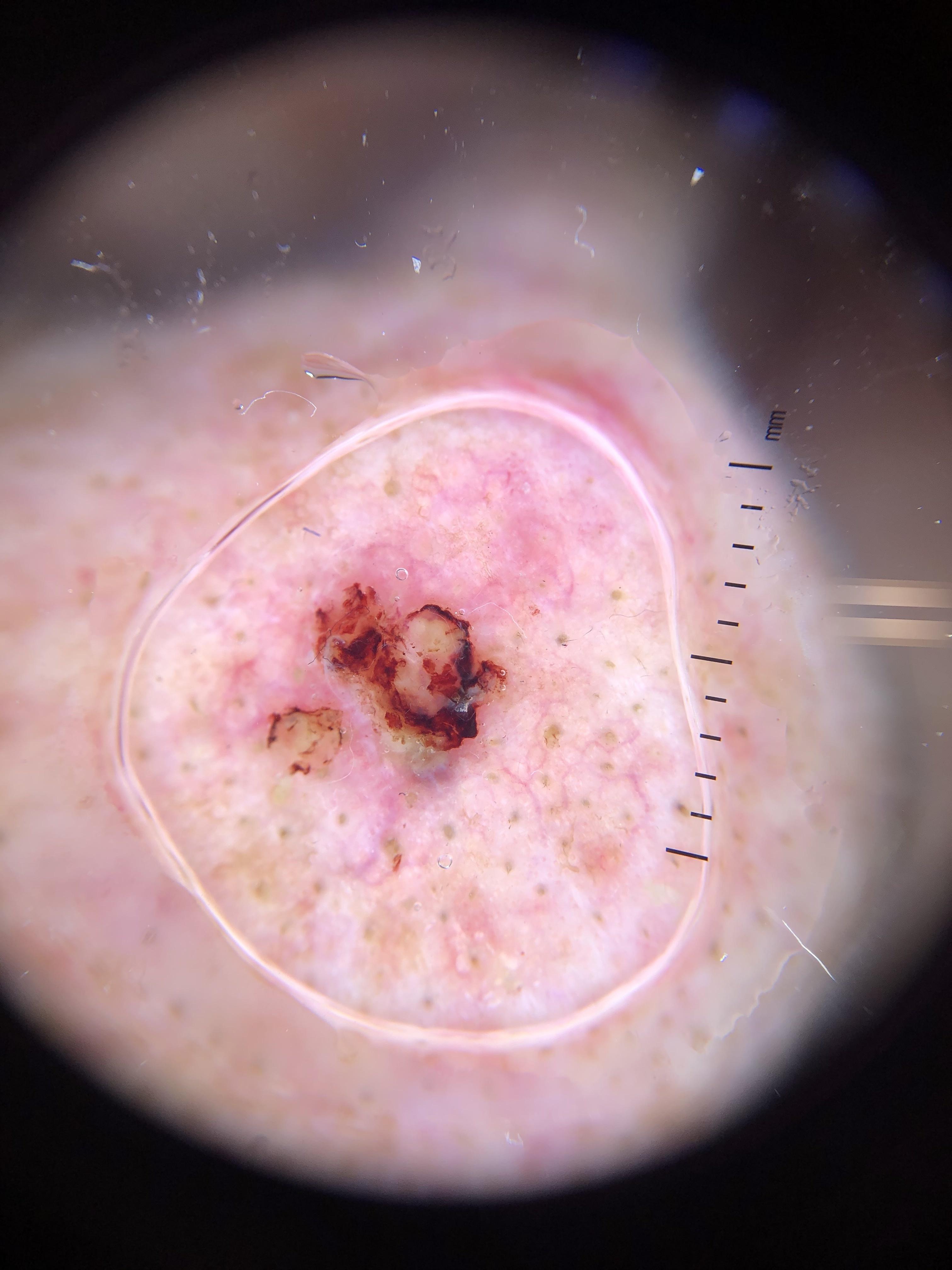Findings:
* diagnosis — Basal cell carcinoma (biopsy-proven)